A contact-polarized dermoscopy image of a skin lesion. A male patient aged 58-62.
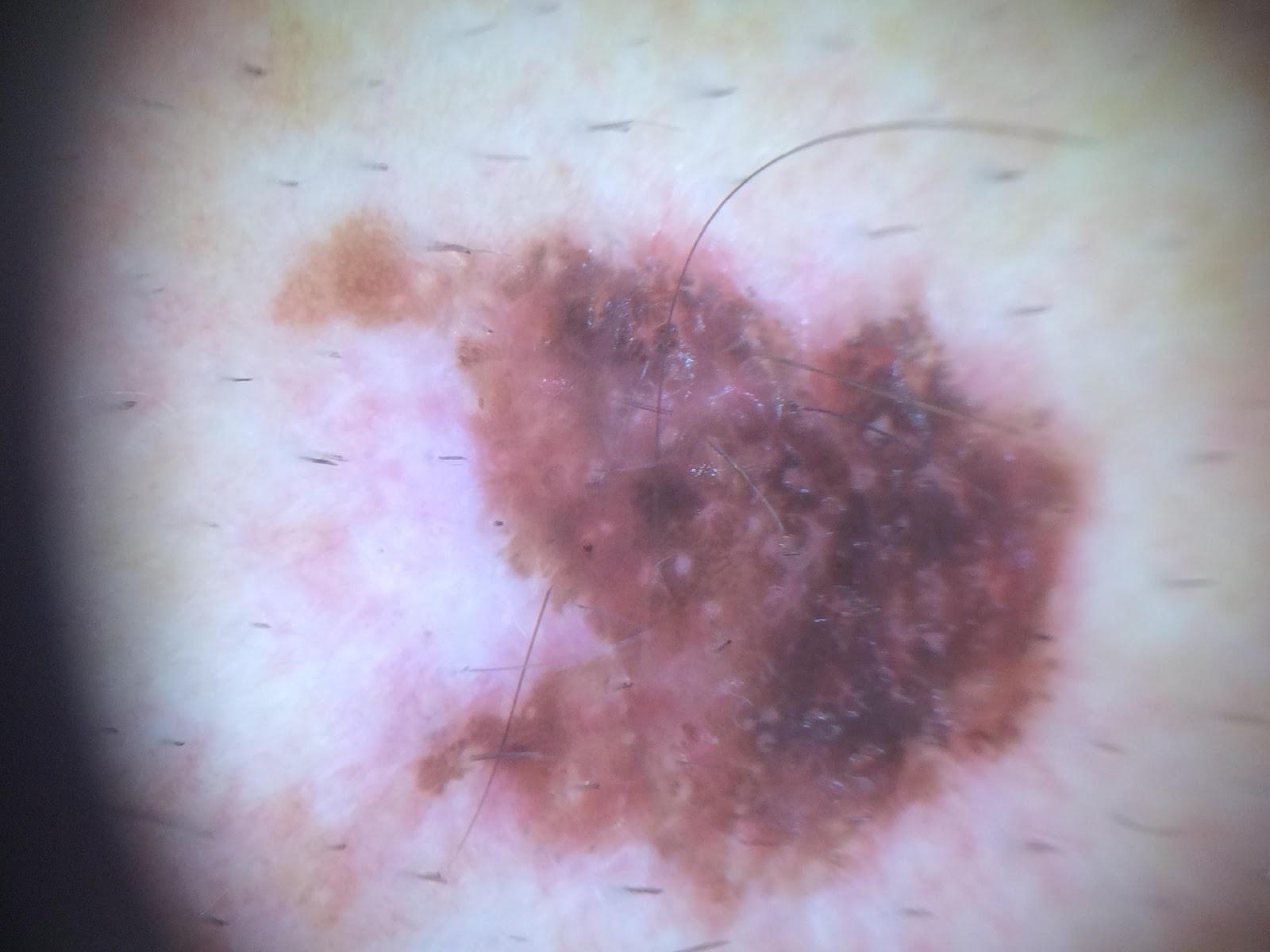Q: What is the anatomic site?
A: the trunk
Q: What did the workup show?
A: Melanoma (biopsy-proven)